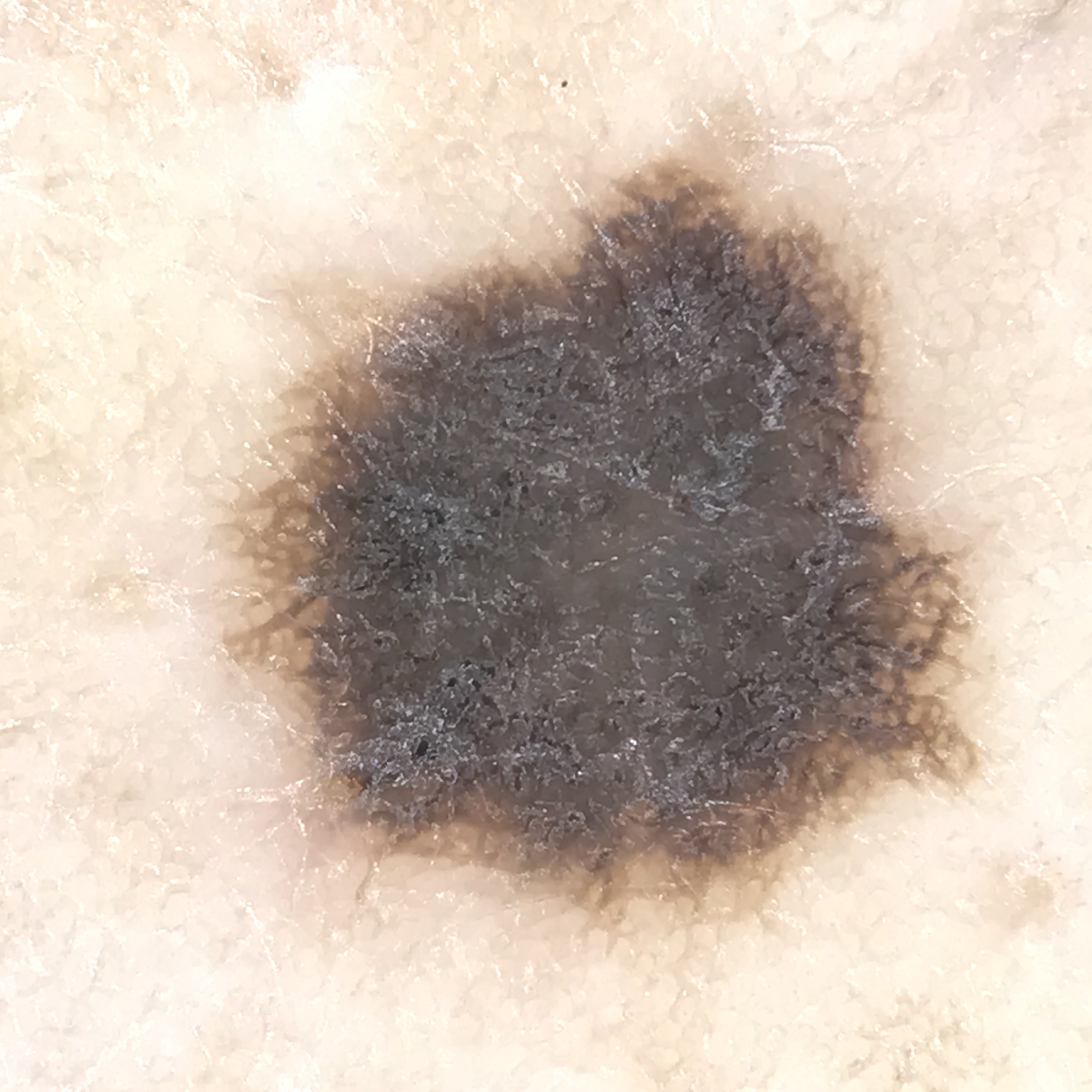<lesion>
<image>dermoscopy</image>
<diagnosis>
<name>dysplastic compound nevus</name>
<code>cd</code>
<malignancy>benign</malignancy>
<super_class>melanocytic</super_class>
<confirmation>expert consensus</confirmation>
</diagnosis>
</lesion>